This is a close-up image. Located on the leg: 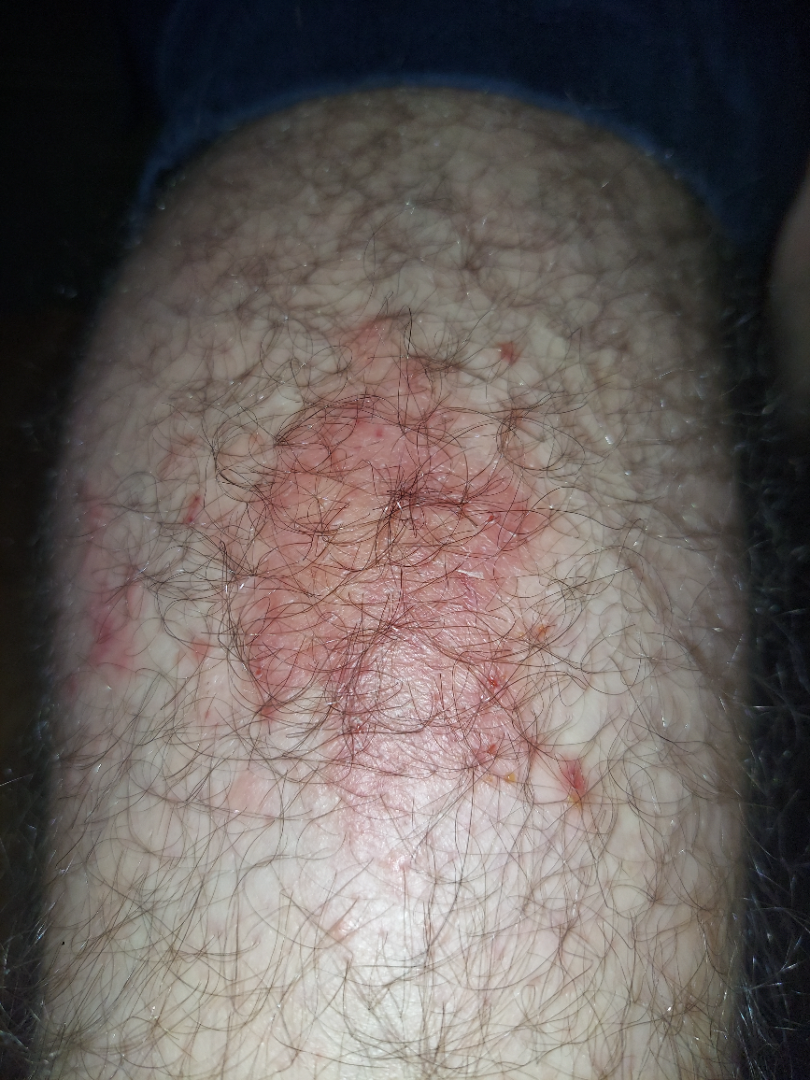Diagnostic features were not clearly distinguishable in this photograph.